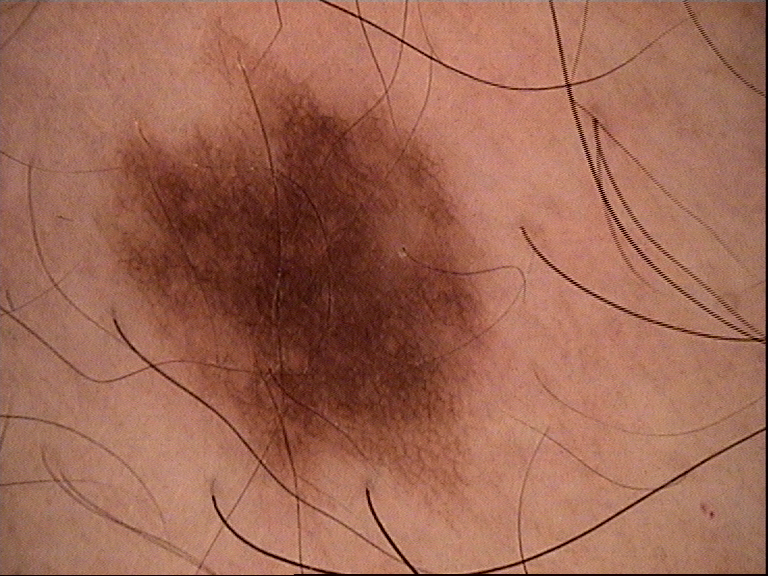image=dermoscopy; class=dysplastic junctional nevus (expert consensus).